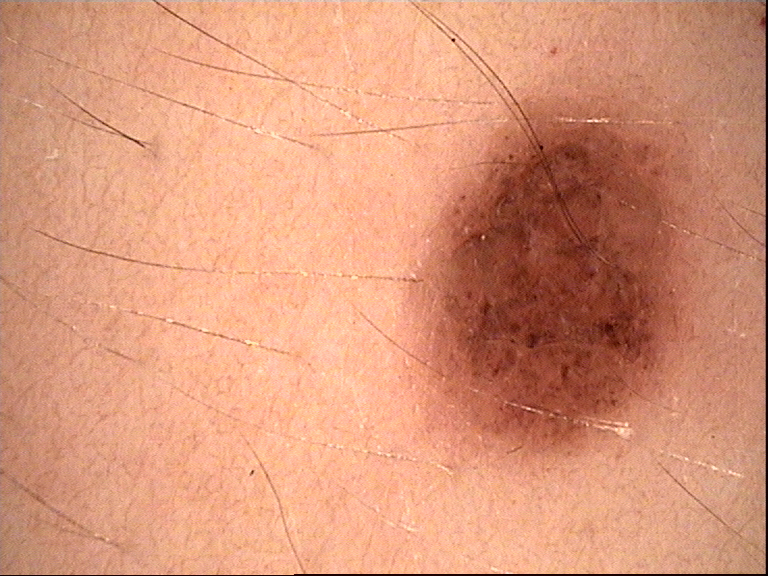Impression: Classified as a dysplastic junctional nevus.